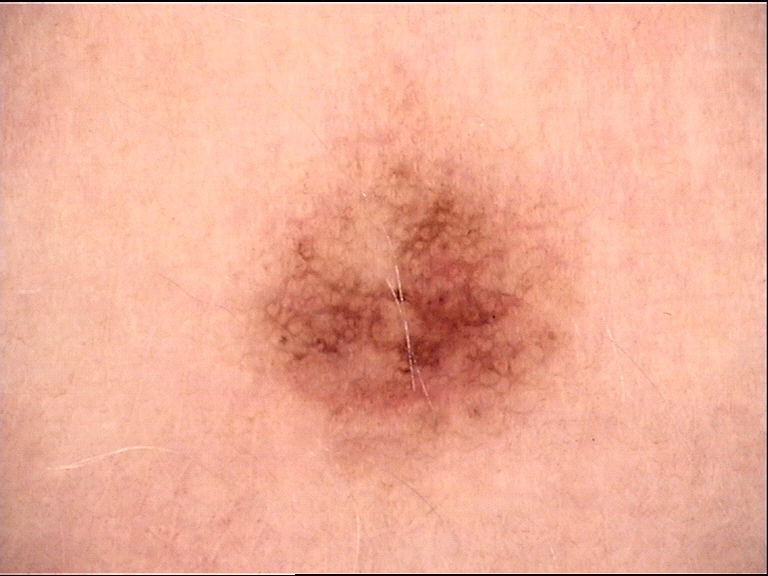A skin lesion imaged with a dermatoscope. Diagnosed as a benign lesion — a dysplastic junctional nevus.